A dermoscopic image of a skin lesion.
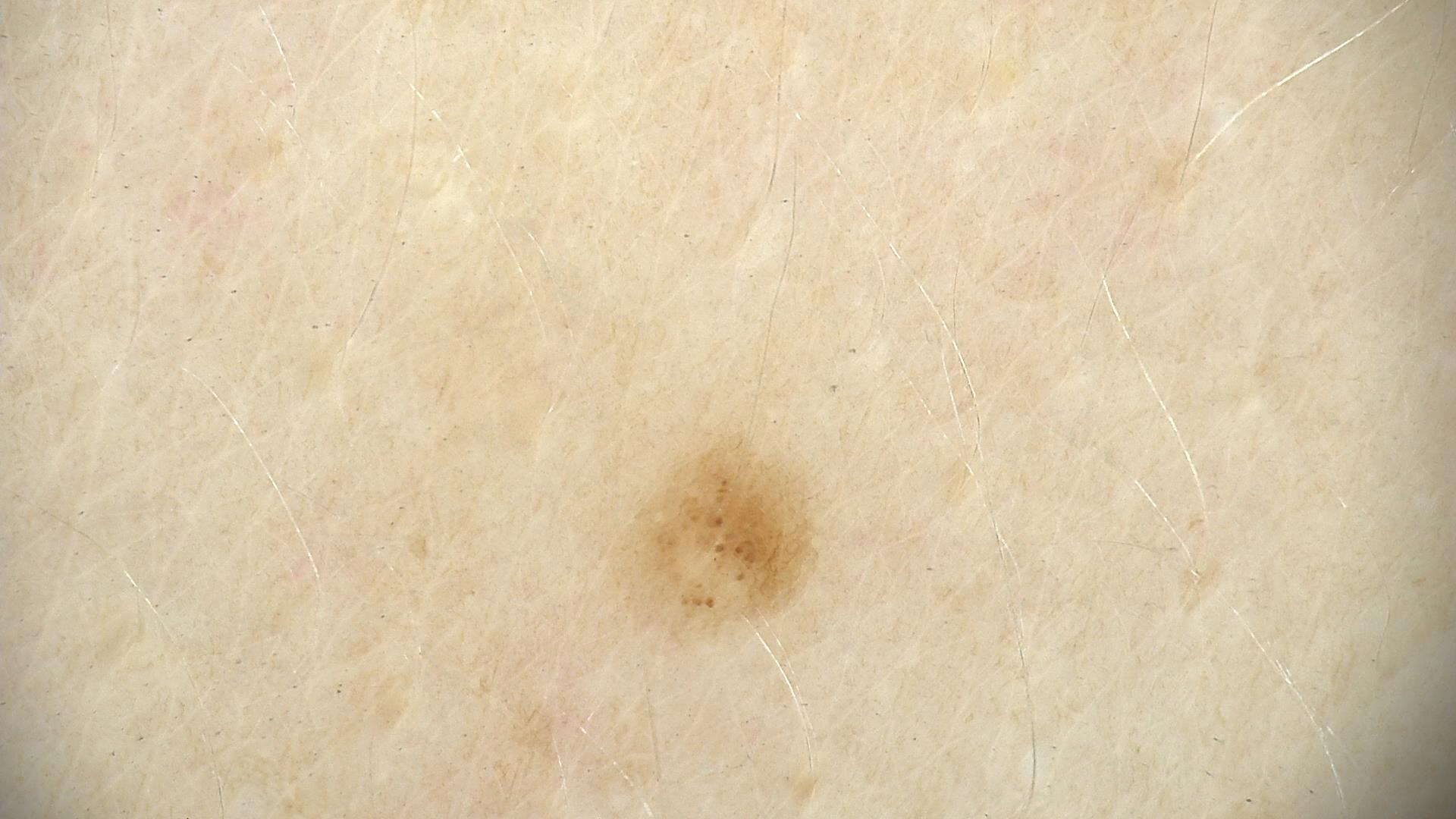The diagnostic label was a benign lesion — a dysplastic junctional nevus.